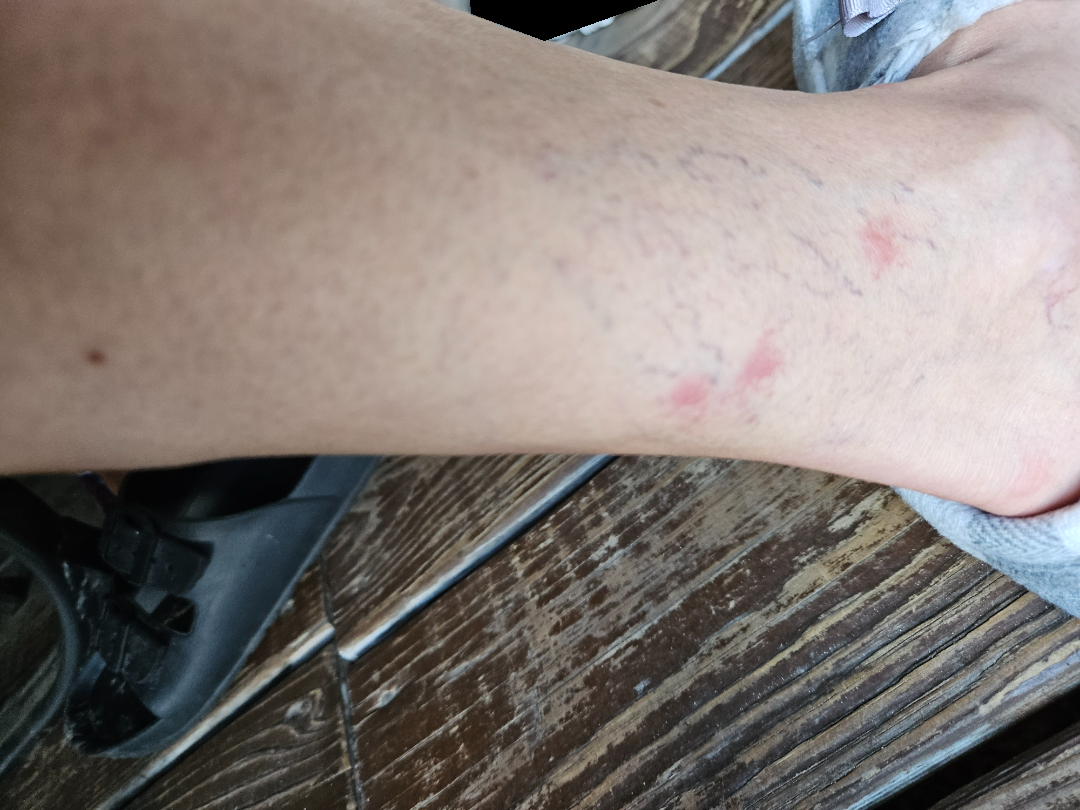differential: Insect Bite (possible); Dermatosis due to flea (possible); Vasculitis of the skin (unlikely).